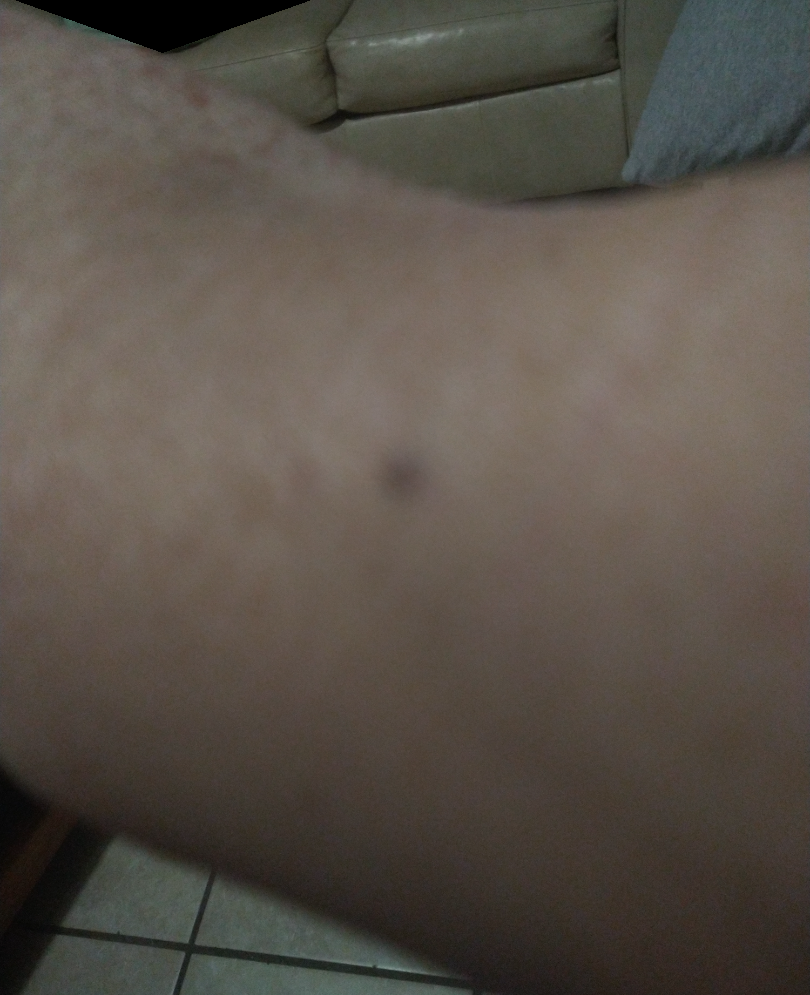{
  "assessment": "indeterminate",
  "symptoms": [
    "itching",
    "pain",
    "burning"
  ],
  "duration": "one to four weeks",
  "body_site": [
    "head or neck",
    "sole of the foot",
    "arm"
  ],
  "systemic_symptoms": "mouth sores",
  "shot_type": "close-up",
  "patient_category": "a rash"
}